A dermoscopy image of a single skin lesion:
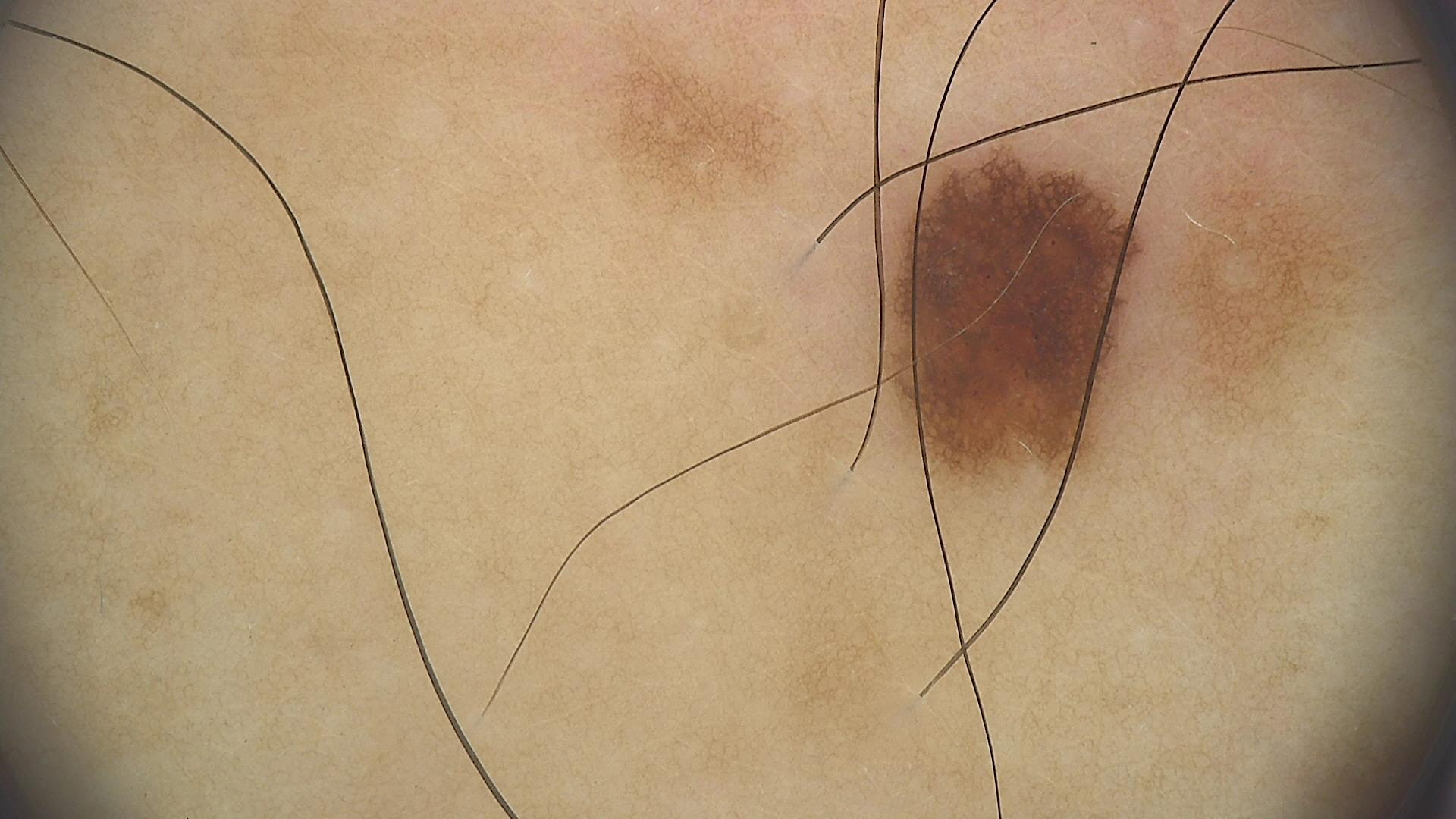Findings:
- label · dysplastic junctional nevus (expert consensus)